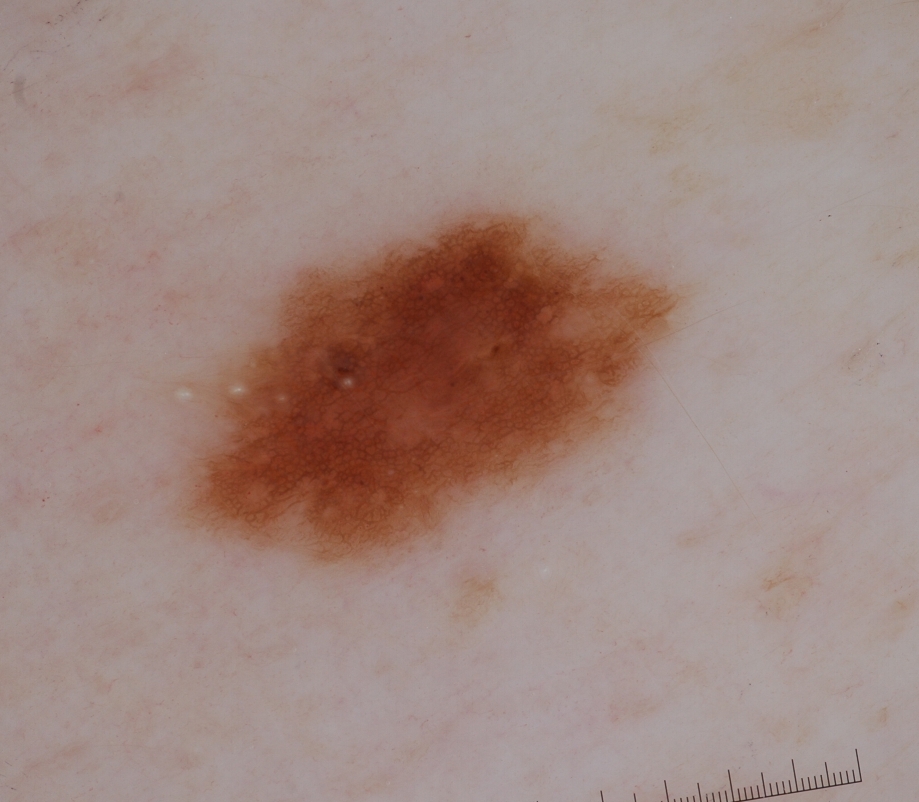image type — dermoscopy of a skin lesion | location — left=154, top=200, right=684, bottom=570 | assessment — a melanocytic nevus.